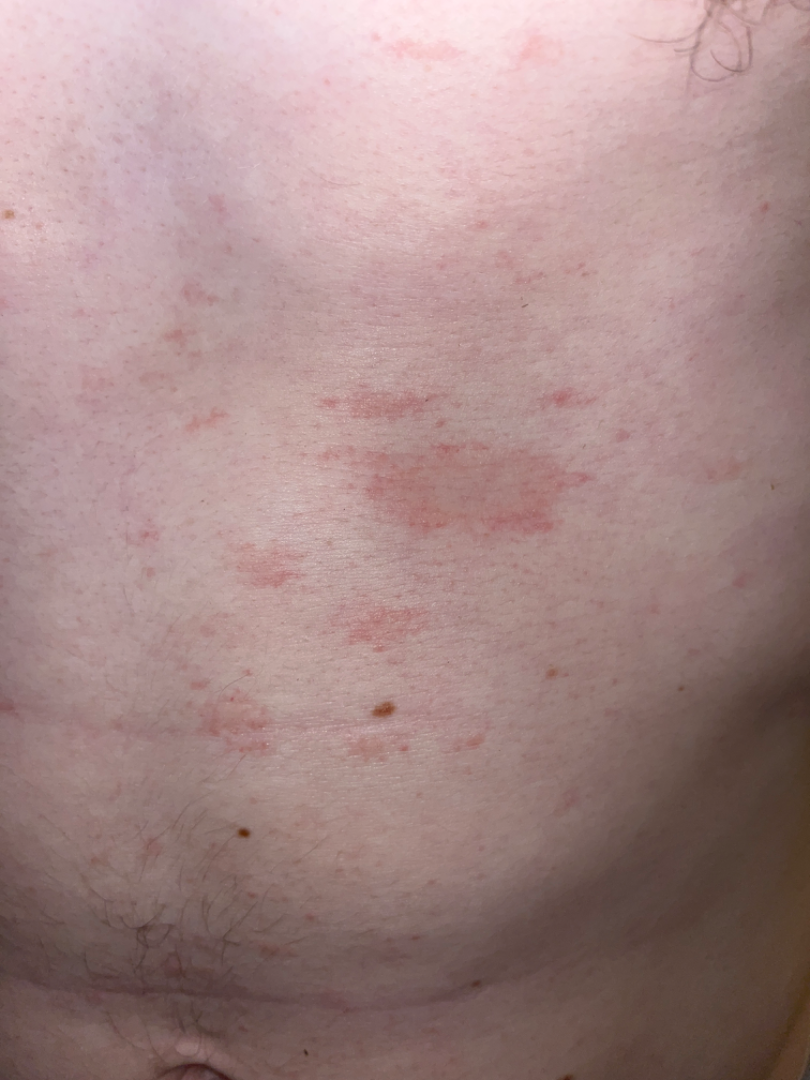The image was not sufficient for the reviewer to characterize the skin condition.